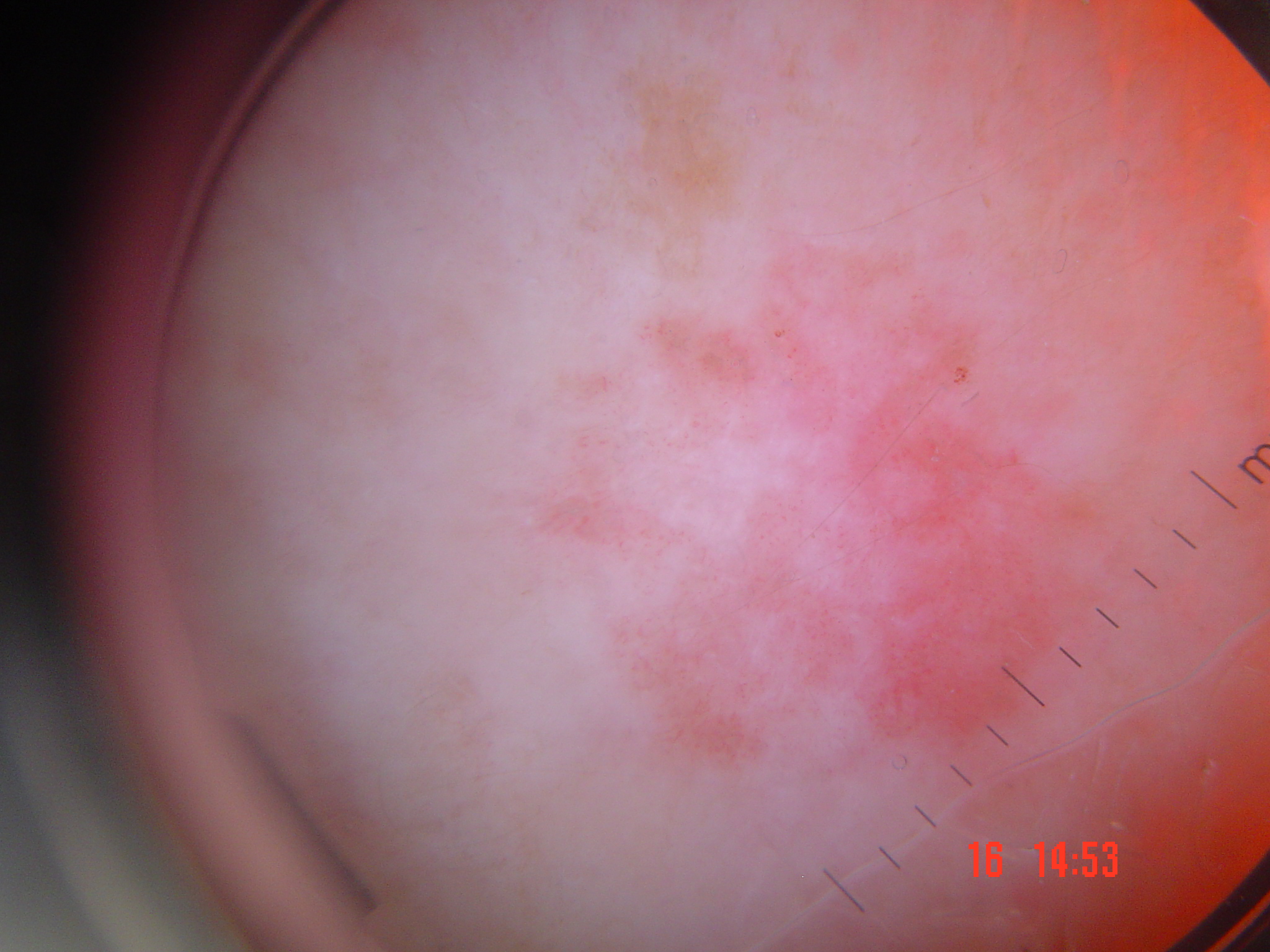diagnostic label — Bowen's disease (biopsy-proven).